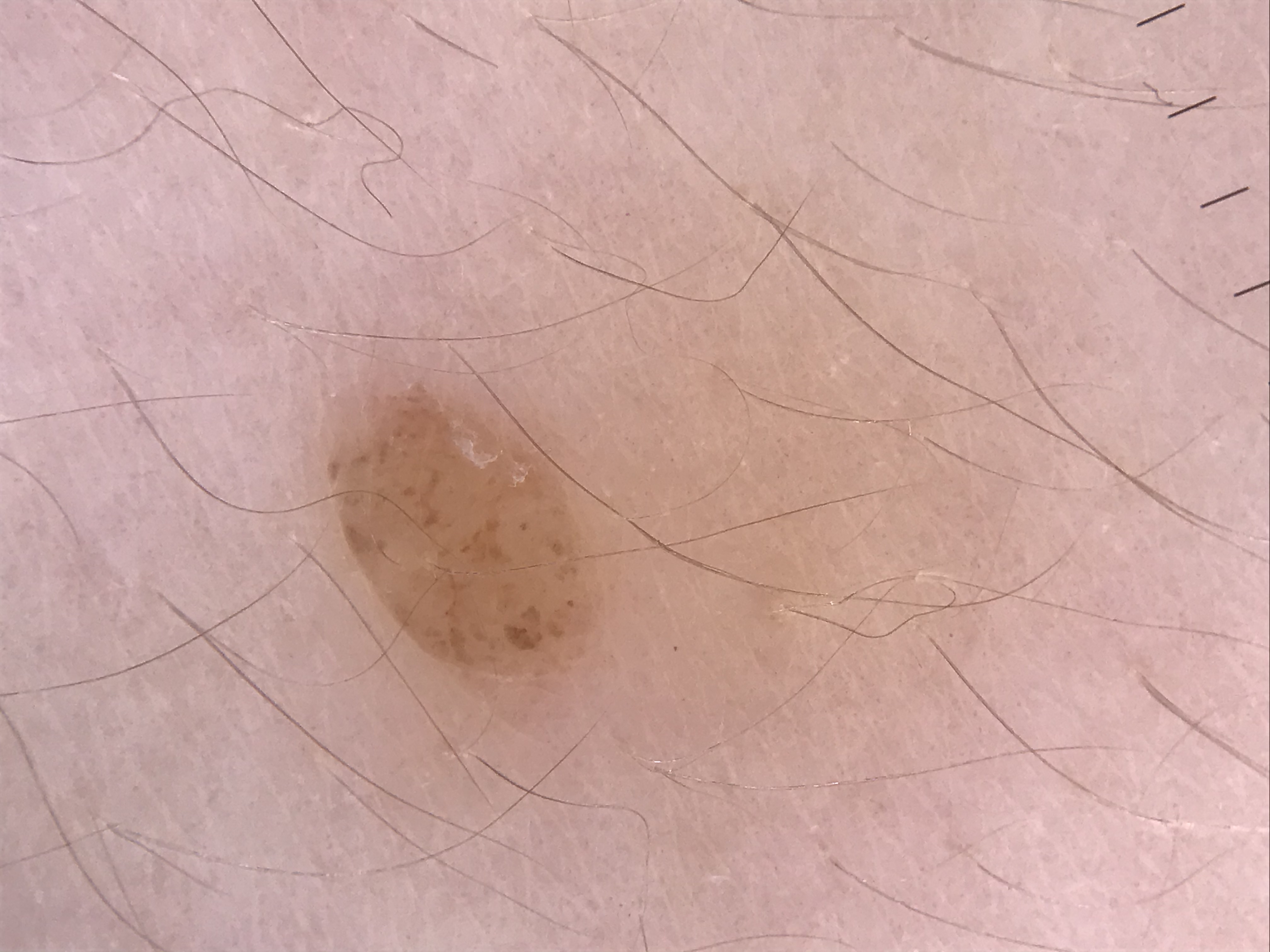A dermoscopic close-up of a skin lesion.
Consistent with a banal lesion — a compound nevus.